The affected area is the arm; the contributor is a female aged 18–29; this is a close-up image.
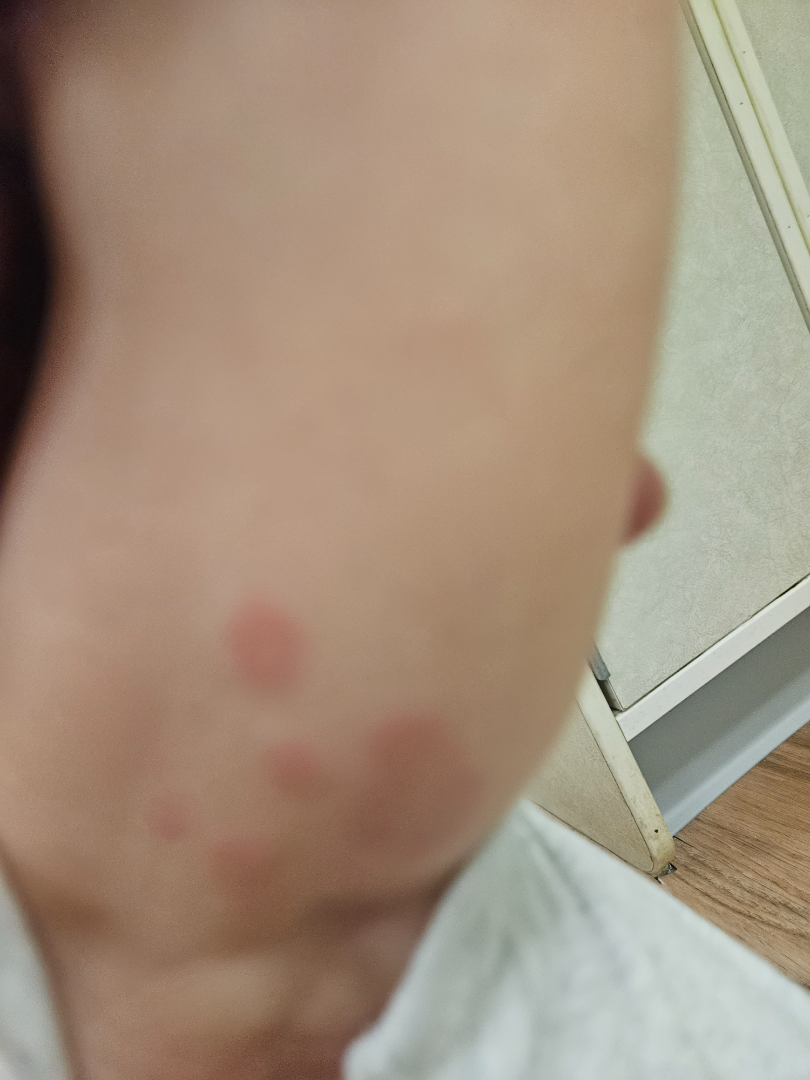The dermatologist could not determine a likely condition from the photograph alone.
The patient considered this a rash.
Fitzpatrick skin type II.